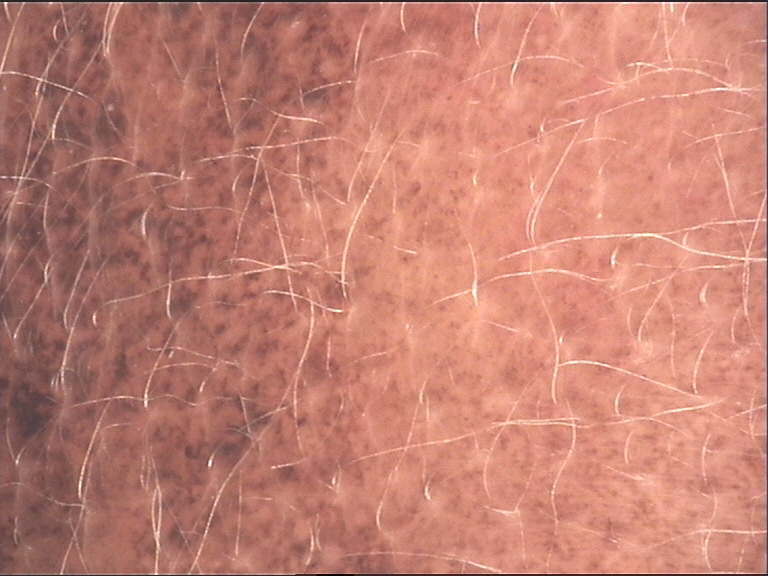– image type · dermatoscopy
– label · congenital compound nevus (expert consensus)